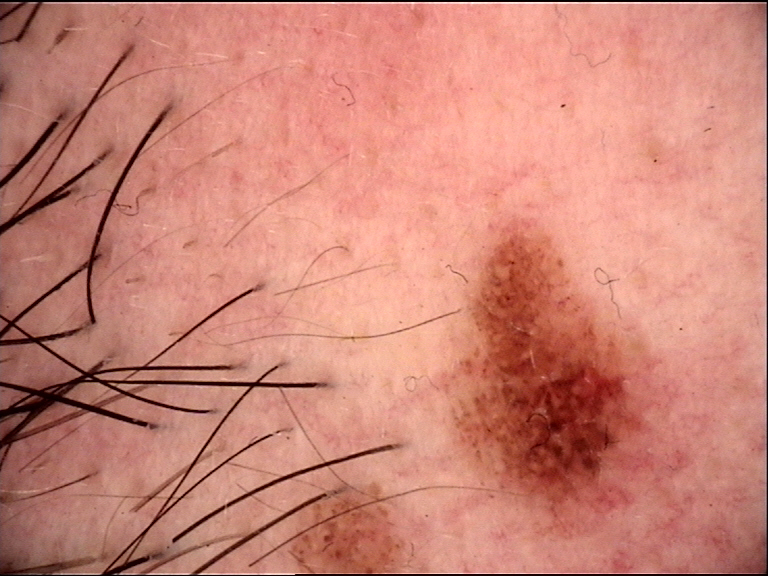The diagnosis was a dysplastic junctional nevus.